The patient indicates the lesion is raised or bumpy and fluid-filled. The affected area is the back of the torso and front of the torso. The condition has been present for less than one week. The patient considered this a rash. Skin tone: Fitzpatrick skin type III. This image was taken at a distance: 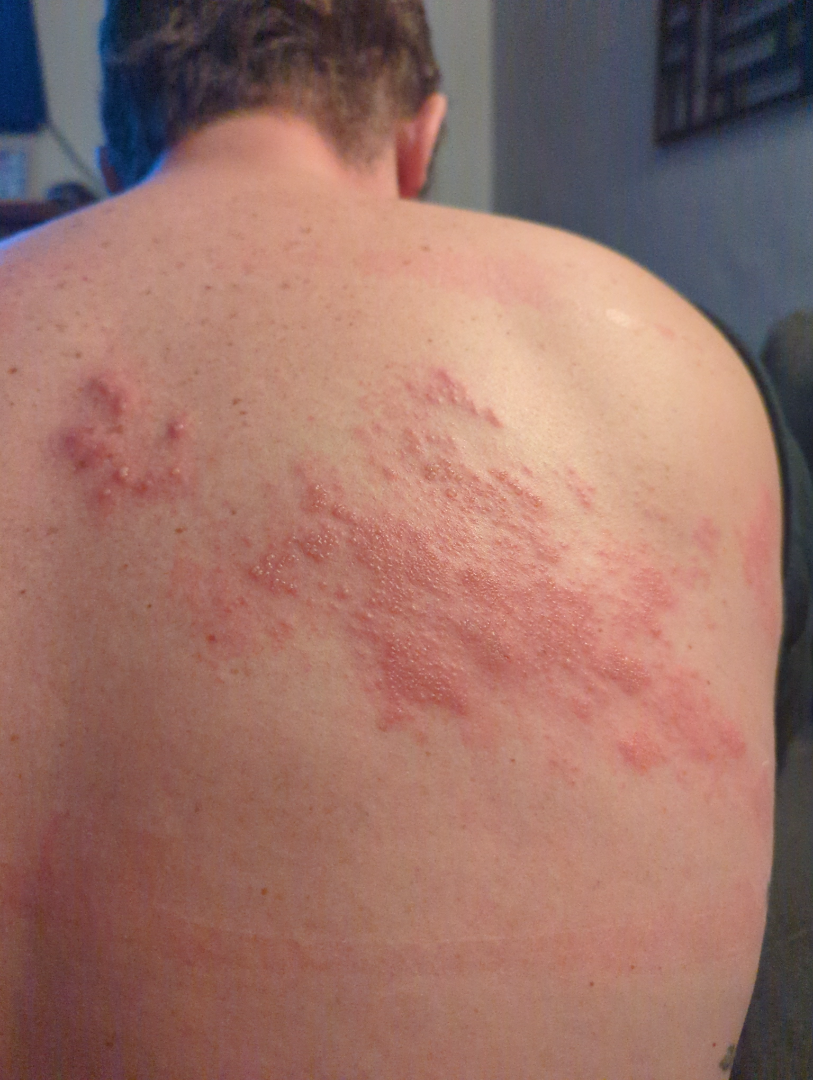impression: the differential is split between Herpes Zoster and Allergic Contact Dermatitis.